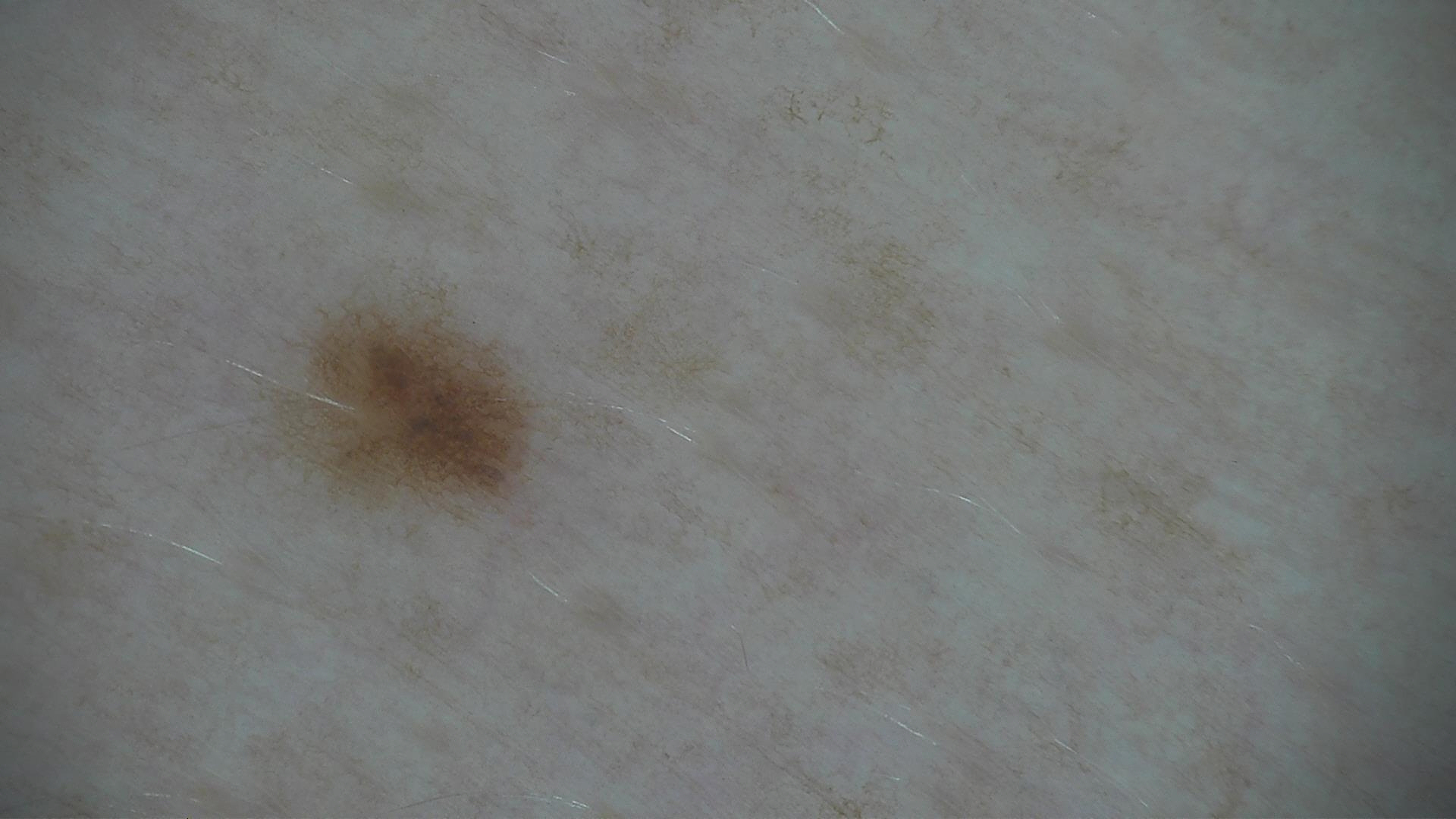Classified as a dysplastic junctional nevus.